The head or neck is involved. Close-up view. Symptoms reported: bothersome appearance. No constitutional symptoms were reported. Female subject, age 40–49. Present for more than five years. The patient reports the lesion is raised or bumpy — 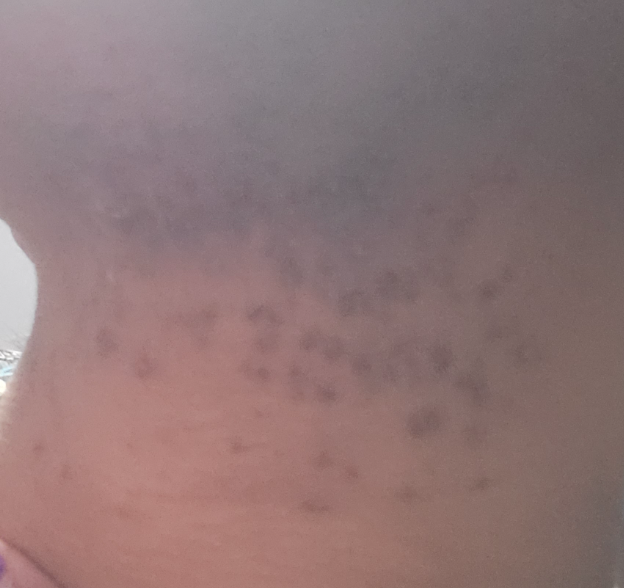{"differential": {"tied_lead": ["Acne", "Folliculitis"]}}